The patient says their skin reddens with sun exposure · acquired for a research image collection, with no referral diagnosis · a moderate number of moles by the patient's own estimate · the patient reports a personal history of cancer and a personal history of skin cancer · a clinical photograph of a skin lesion.
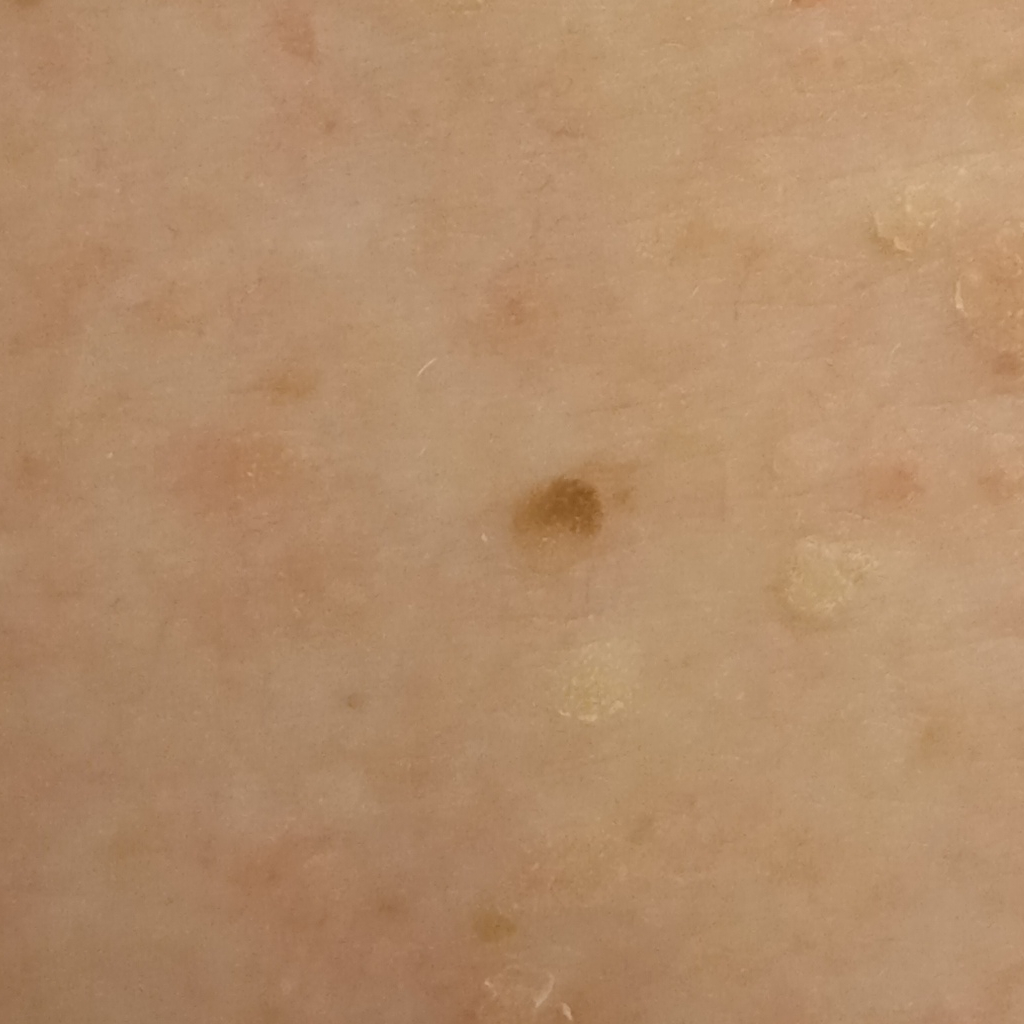Case summary: The lesion is on the back. Measuring roughly 3 mm. Assessment: The diagnostic impression was a seborrheic keratosis.